A dermoscopic close-up of a skin lesion:
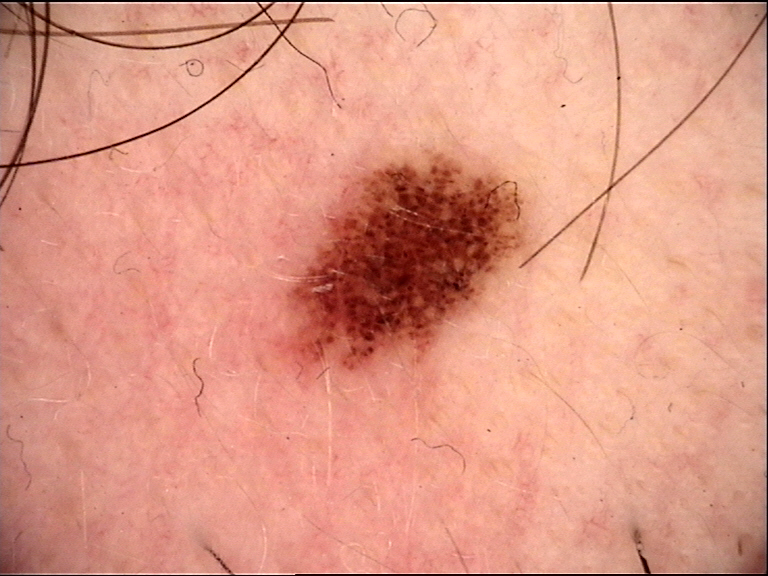This is a banal lesion. Classified as a junctional nevus.